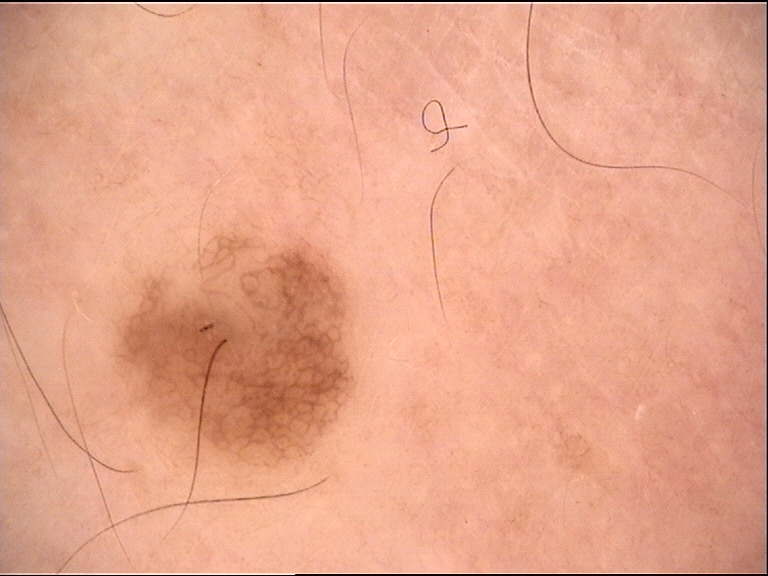Dermoscopy of a skin lesion. The diagnosis was a compound nevus.